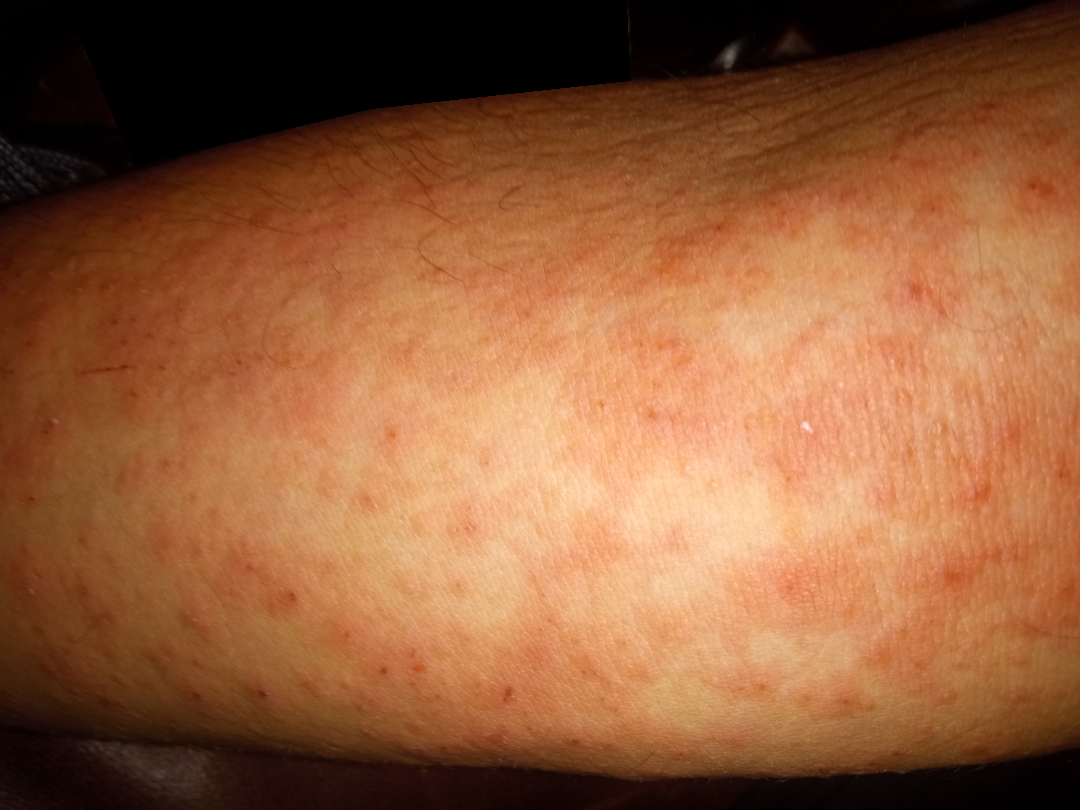Q: What was the assessment?
A: unable to determine
Q: Texture?
A: raised or bumpy and rough or flaky
Q: Reported symptoms?
A: bothersome appearance, itching, enlargement, burning and darkening
Q: Who is the patient?
A: male, age 40–49
Q: How does the patient describe it?
A: a rash
Q: How long has this been present?
A: less than one week
Q: Image view?
A: at an angle
Q: What is the affected area?
A: leg, arm, front of the torso and back of the torso